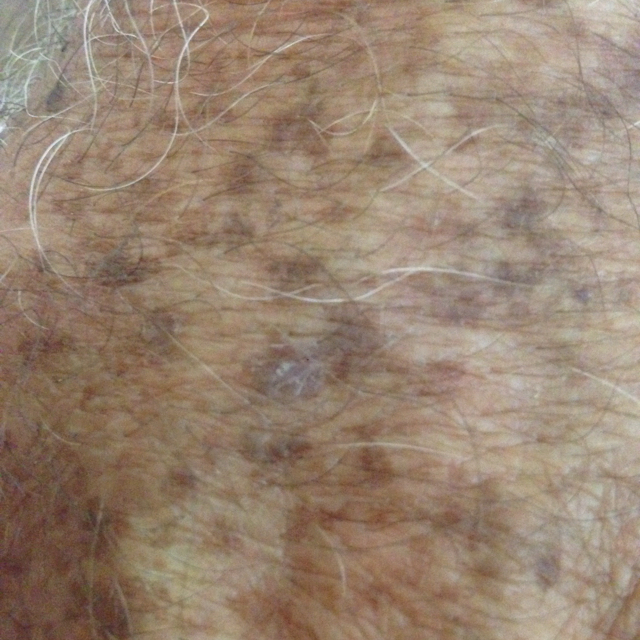image type=clinical photograph
subject=55 years of age
location=a hand
patient-reported symptoms=growth, change in appearance, elevation
diagnosis=actinic keratosis (clinical consensus)